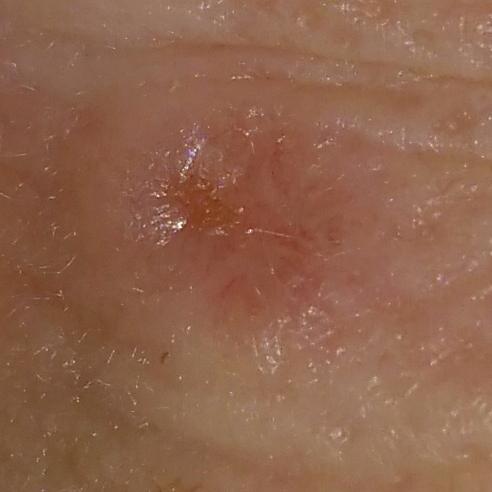imaging = clinical photograph; subject = female, 68 years of age; location = the nose; diameter = 4 × 4 mm; diagnostic label = basal cell carcinoma (biopsy-proven).